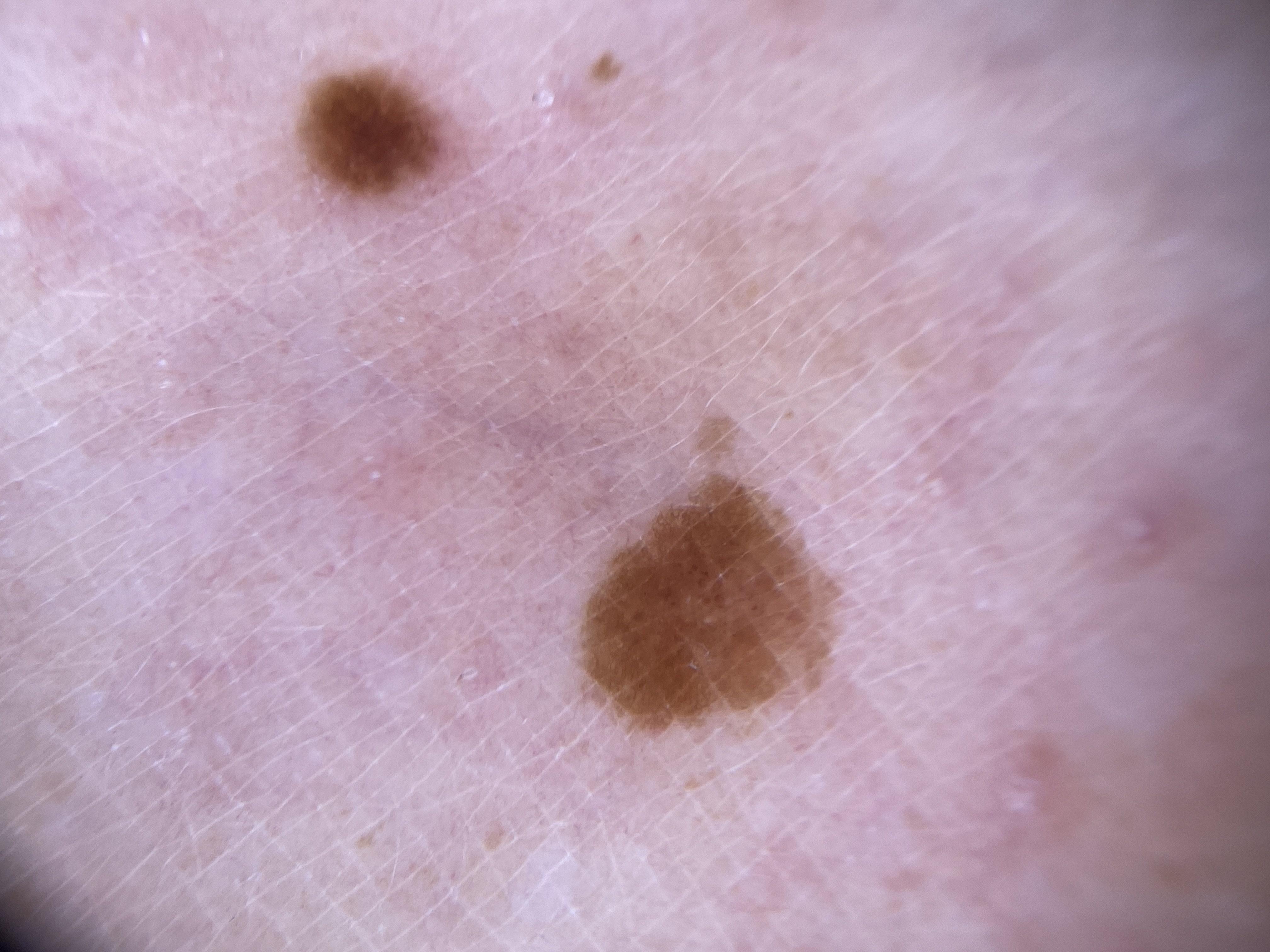impression: Nevus.